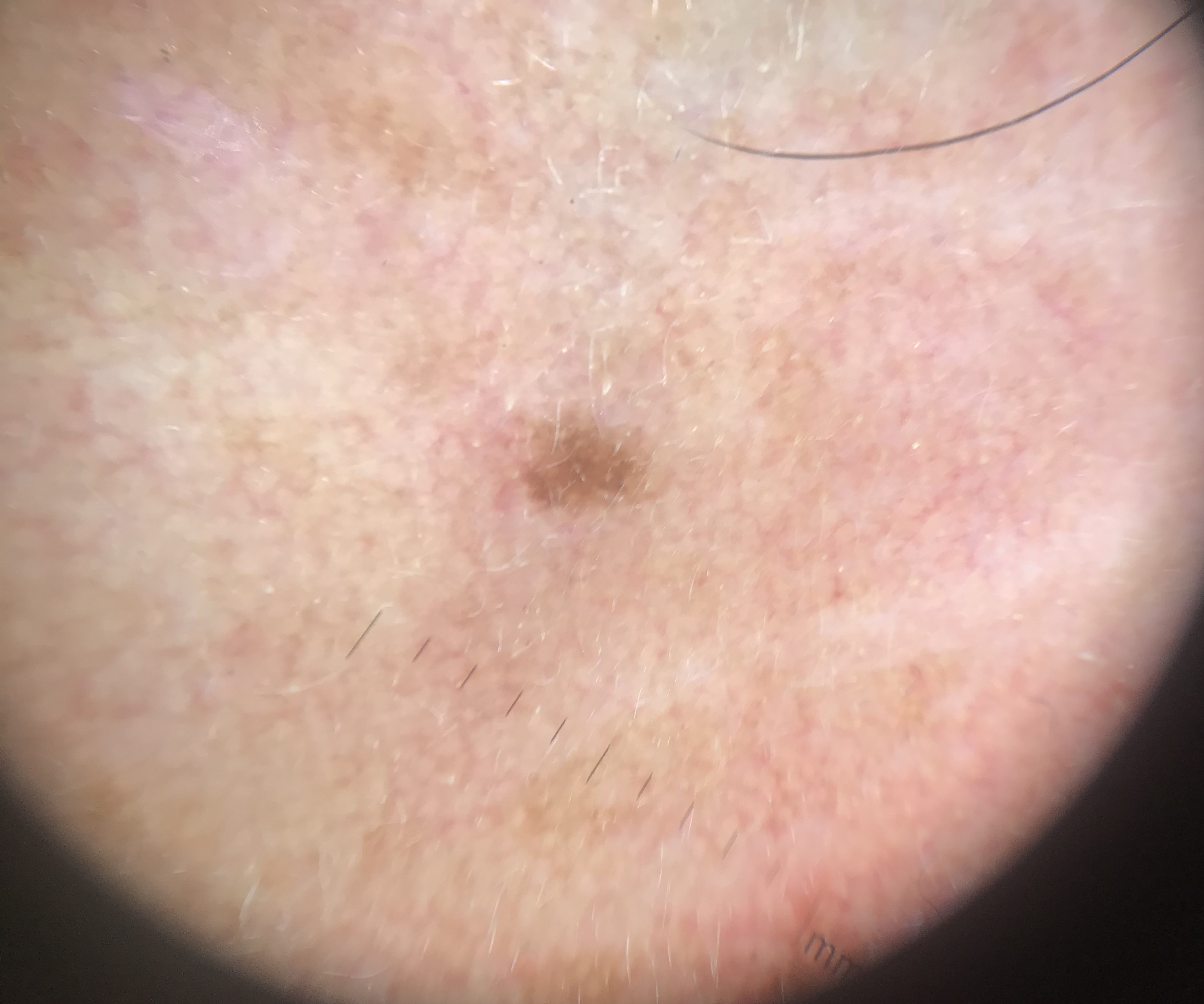Case:
• lesion type — keratinocytic
• label — seborrheic keratosis (expert consensus)